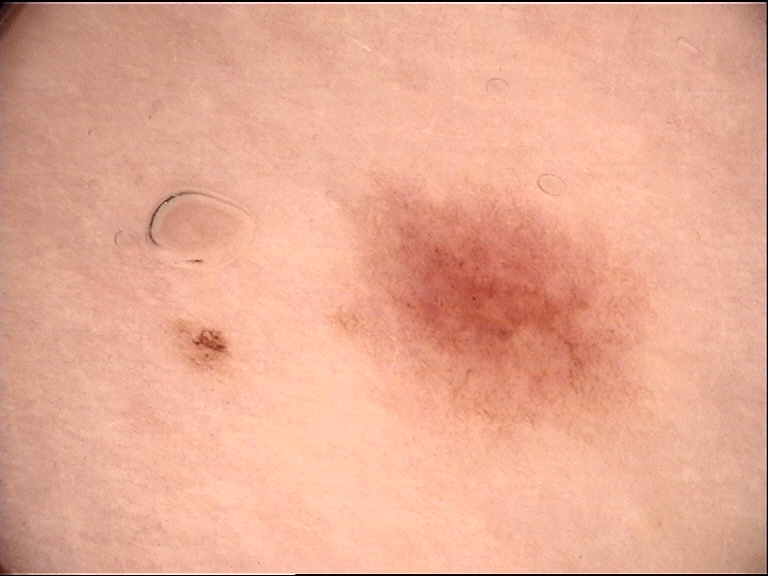{
  "image": "dermatoscopy",
  "diagnosis": {
    "name": "dysplastic junctional nevus",
    "code": "jd",
    "malignancy": "benign",
    "super_class": "melanocytic",
    "confirmation": "expert consensus"
  }
}